A dermoscopic image of a skin lesion.
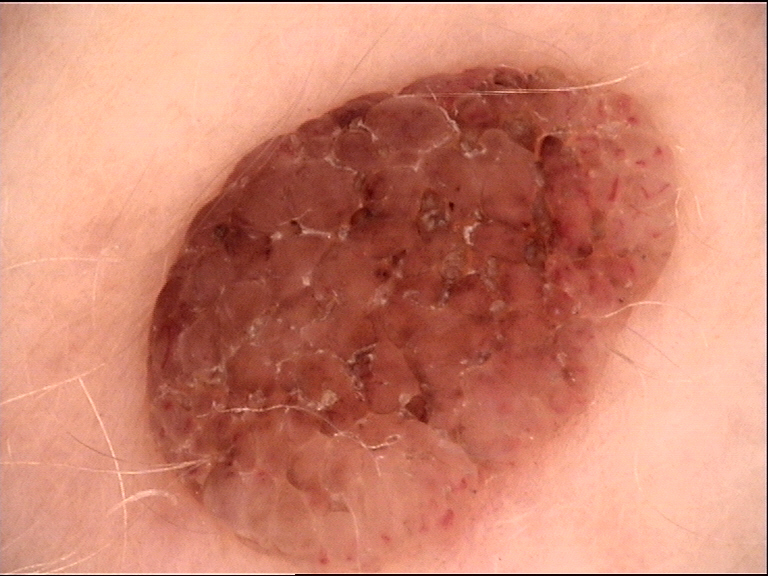  lesion_type:
    main_class: banal
    pattern: dermal
  diagnosis:
    name: dermal nevus
    code: db
    malignancy: benign
    super_class: melanocytic
    confirmation: expert consensus